The contributor is a female aged 50–59, this is a close-up image, the lesion involves the arm — 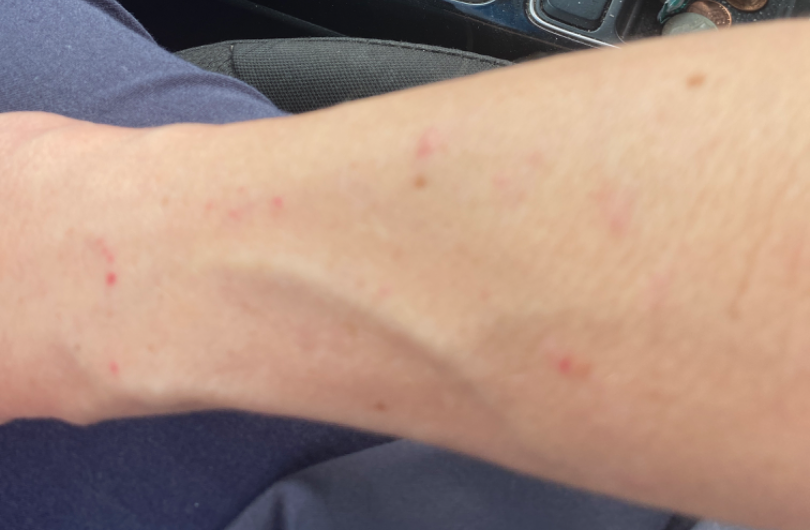– assessment — ungradable on photographic review